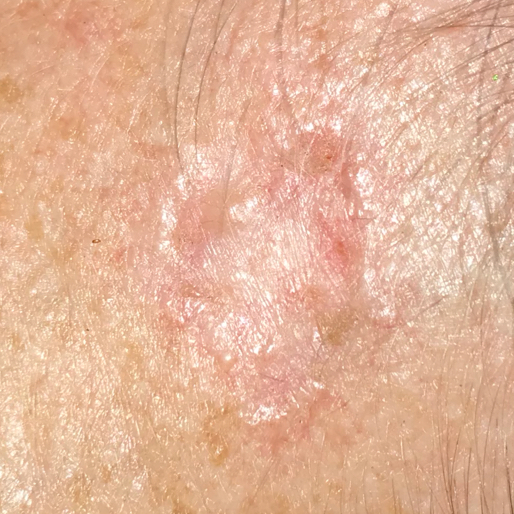A female subject in their early 50s.
A clinical photo of a skin lesion taken with a smartphone.
History notes prior malignancy (patient or family) and alcohol use.
Skin type III.
Located on the face.
Measuring about 15 × 10 mm.
The patient describes that the lesion has changed, is elevated, has bled, and has grown, but does not itch.
The biopsy diagnosis was a malignant lesion — a basal cell carcinoma.